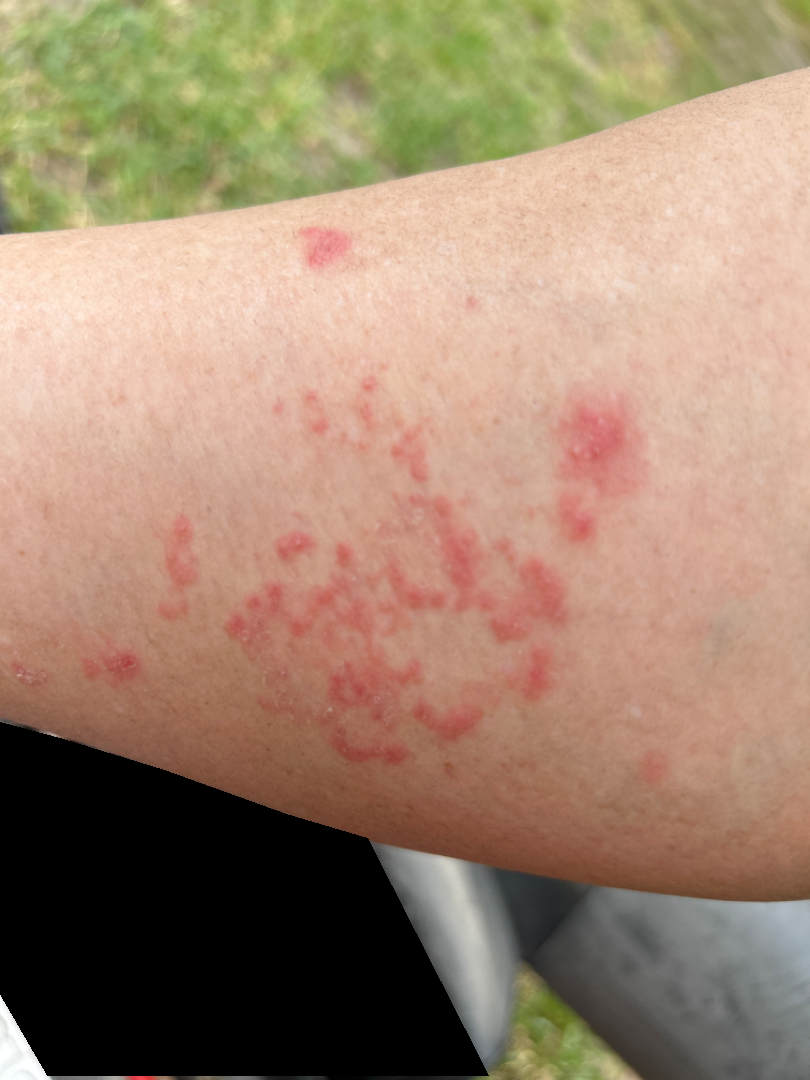Impression: Eczema and Allergic Contact Dermatitis were each considered, in no particular order; a more distant consideration is Psoriasis.